A dermoscopic close-up of a skin lesion.
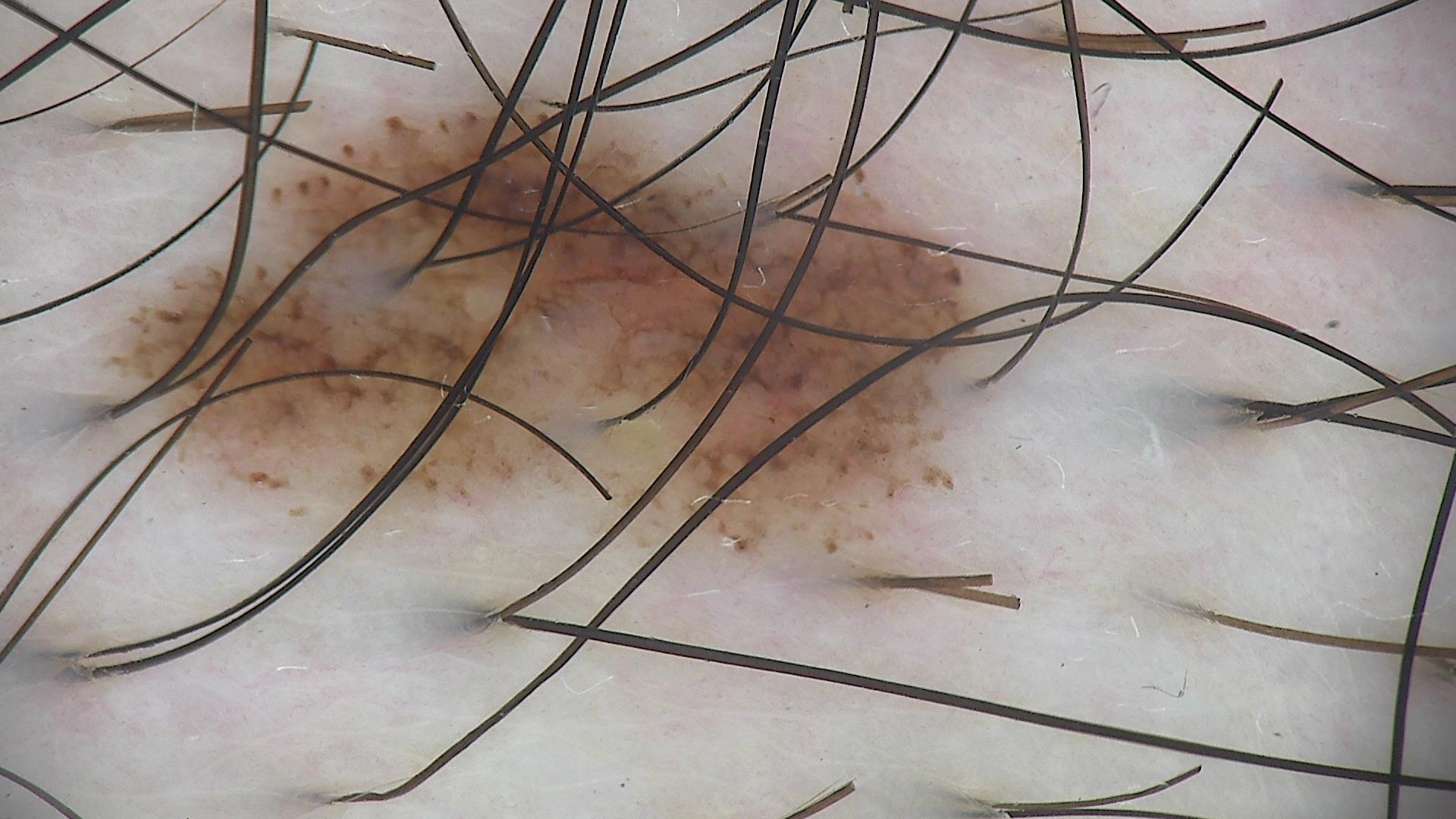Impression:
Classified as a benign lesion — a dysplastic junctional nevus.